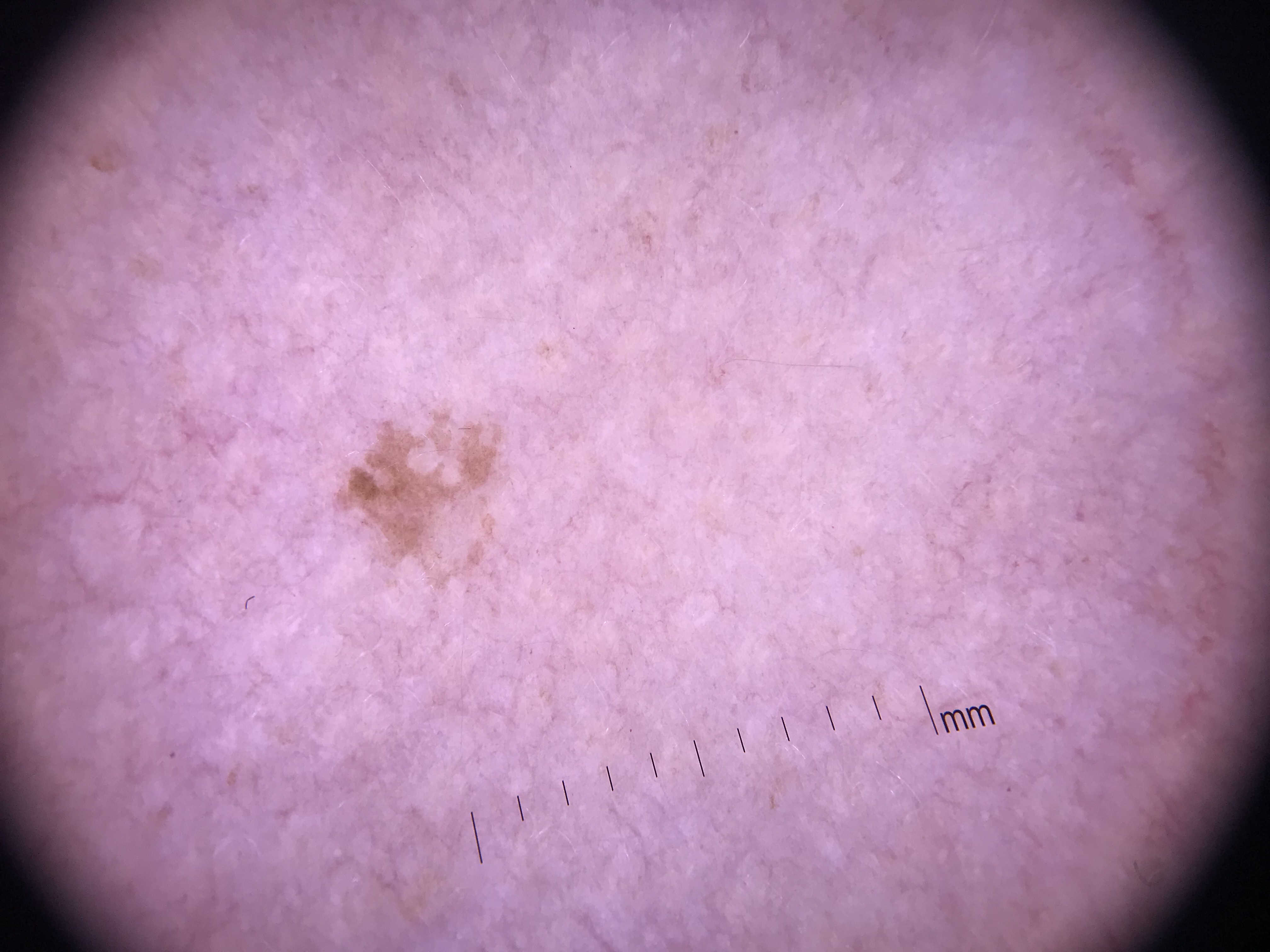A dermoscopy image of a single skin lesion.
Consistent with a keratinocytic lesion — a seborrheic keratosis.